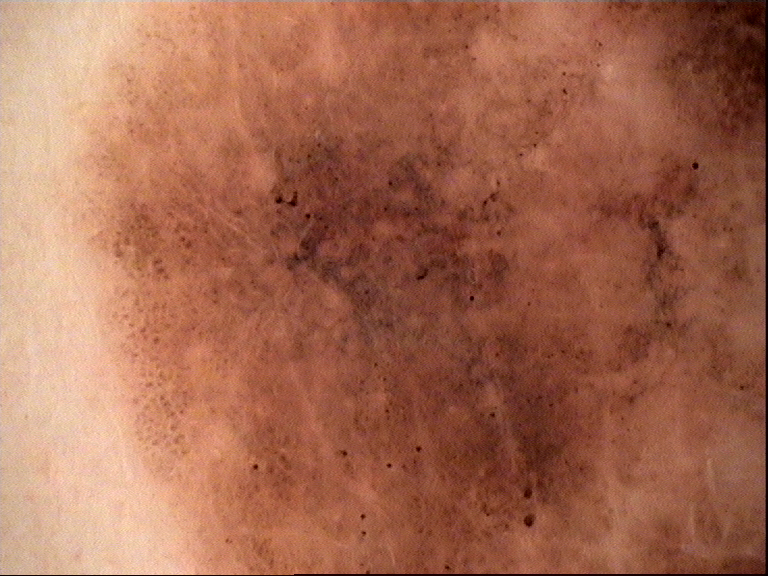Findings:
– modality · dermatoscopy
– diagnosis · acral lentiginous melanoma (biopsy-proven)